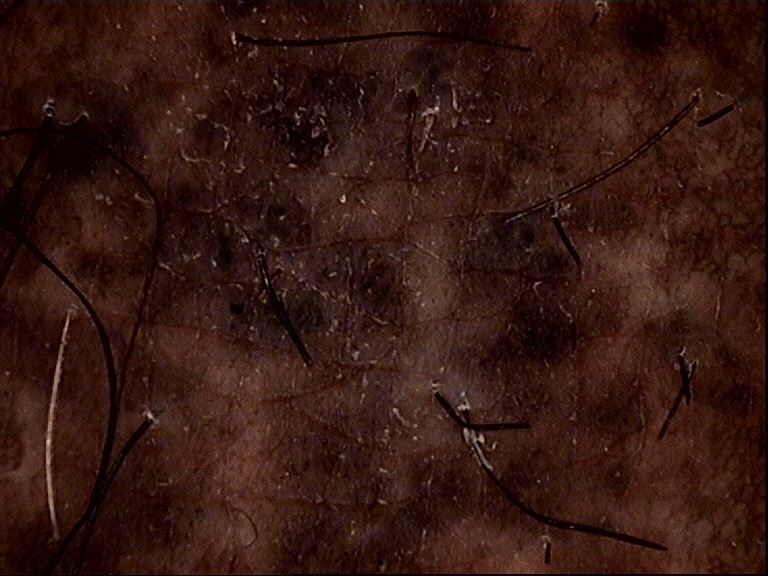Impression:
The diagnostic label was a congenital compound nevus.